A female subject, in their mid- to late 70s; a dermoscopic image of a skin lesion:
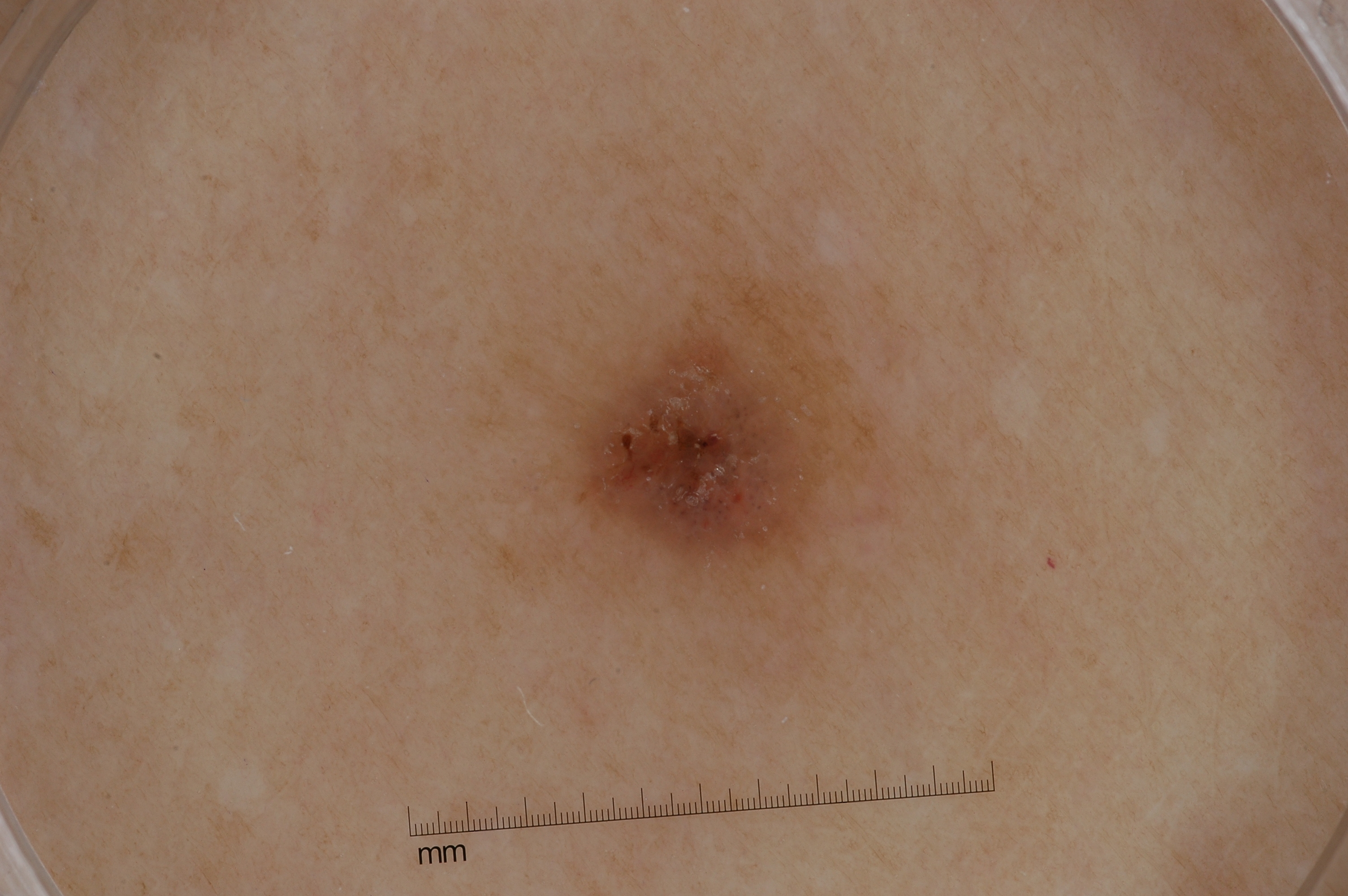The dermoscopic pattern shows no negative network, pigment network, milia-like cysts, or streaks.
The lesion covers approximately 9% of the dermoscopic field.
In (x1, y1, x2, y2) order, lesion location: [506, 238, 916, 644].
Consistent with a seborrheic keratosis, a keratinocytic lesion.